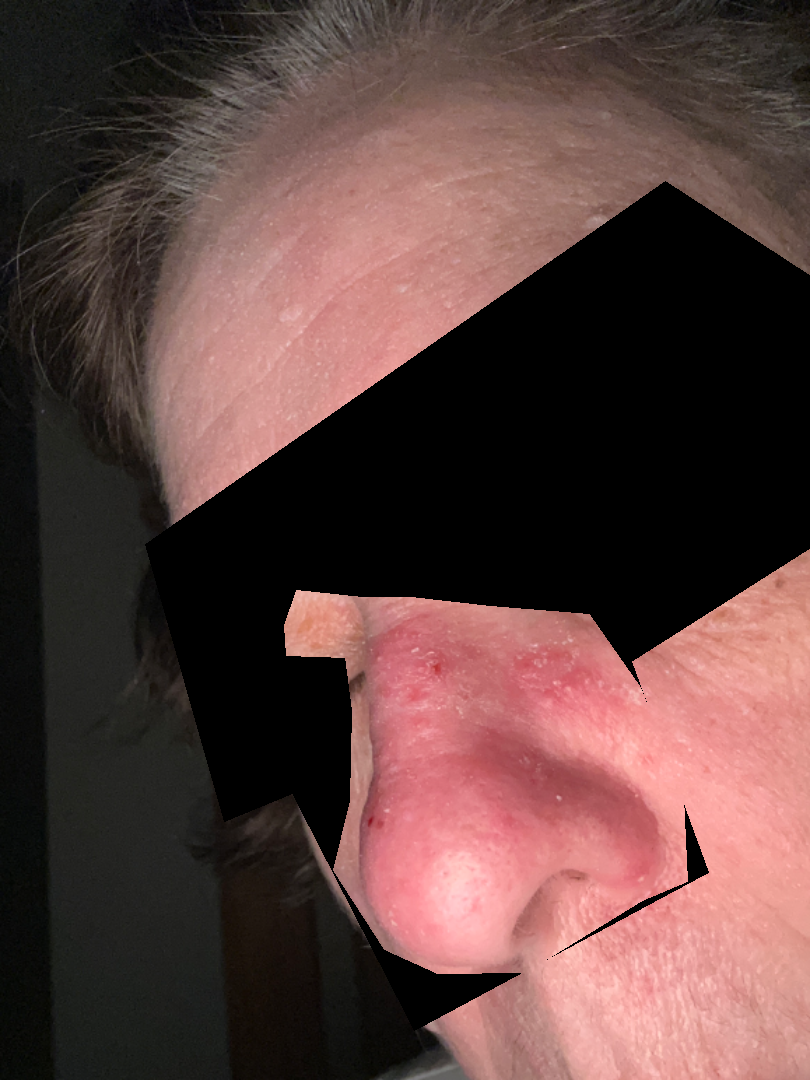Patient information: The patient reported no relevant symptoms from the lesion. The photograph was taken at an angle. The contributor reports the lesion is raised or bumpy. Located on the head or neck. Review: The reviewing clinician's impression was: in keeping with Actinic Keratosis.